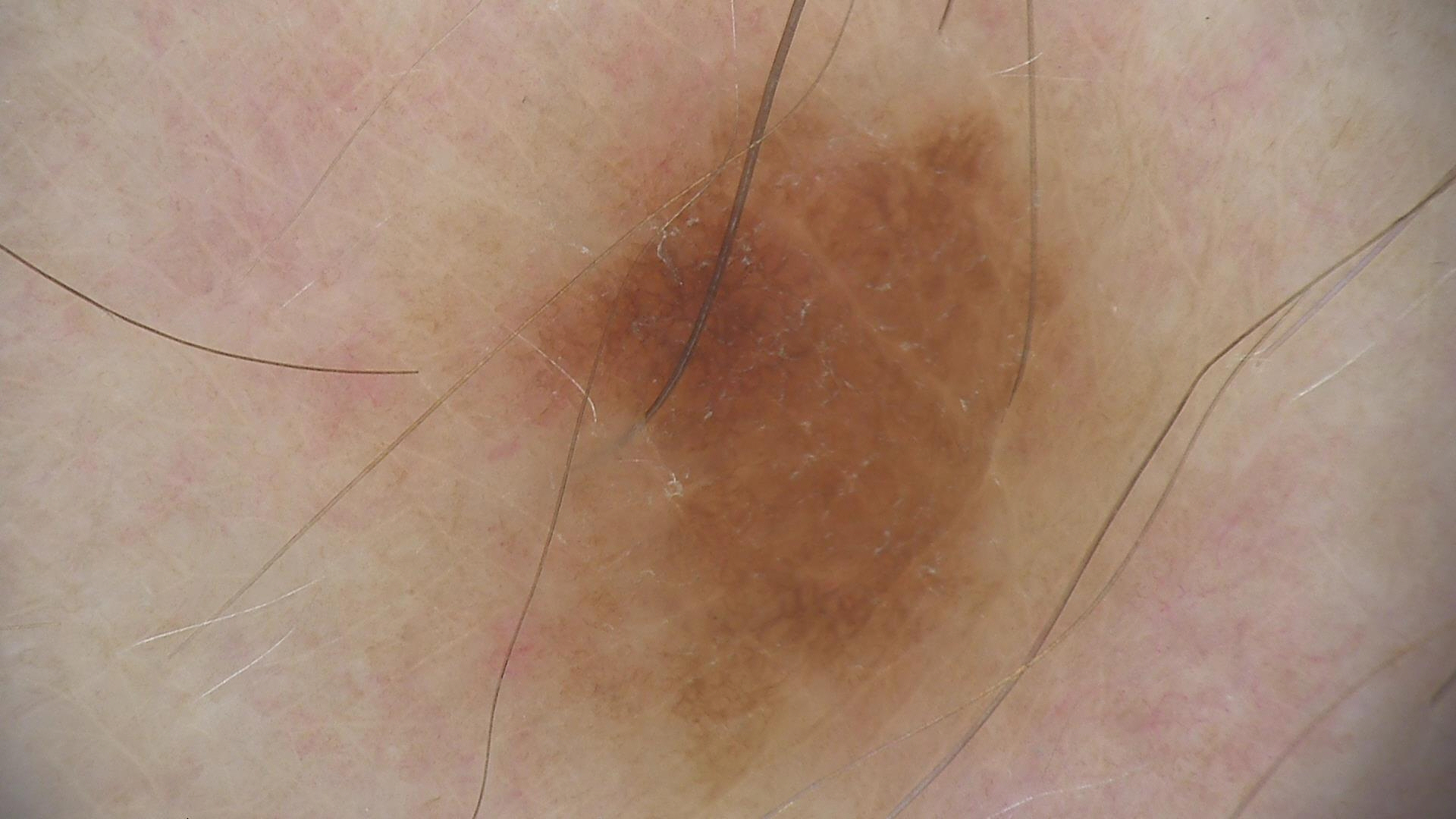<lesion>
  <image>dermoscopy</image>
  <diagnosis>
    <name>dysplastic junctional nevus</name>
    <code>jd</code>
    <malignancy>benign</malignancy>
    <super_class>melanocytic</super_class>
    <confirmation>expert consensus</confirmation>
  </diagnosis>
</lesion>